The contributor is a female aged 40–49. The lesion is described as raised or bumpy, fluid-filled and rough or flaky. Self-categorized by the patient as a rash. The patient reports the condition has been present for more than one year. The affected area is the leg and arm. An image taken at an angle. The patient also reports chills, fatigue and joint pain. Reported lesion symptoms include enlargement, pain, bleeding, darkening, burning and itching:
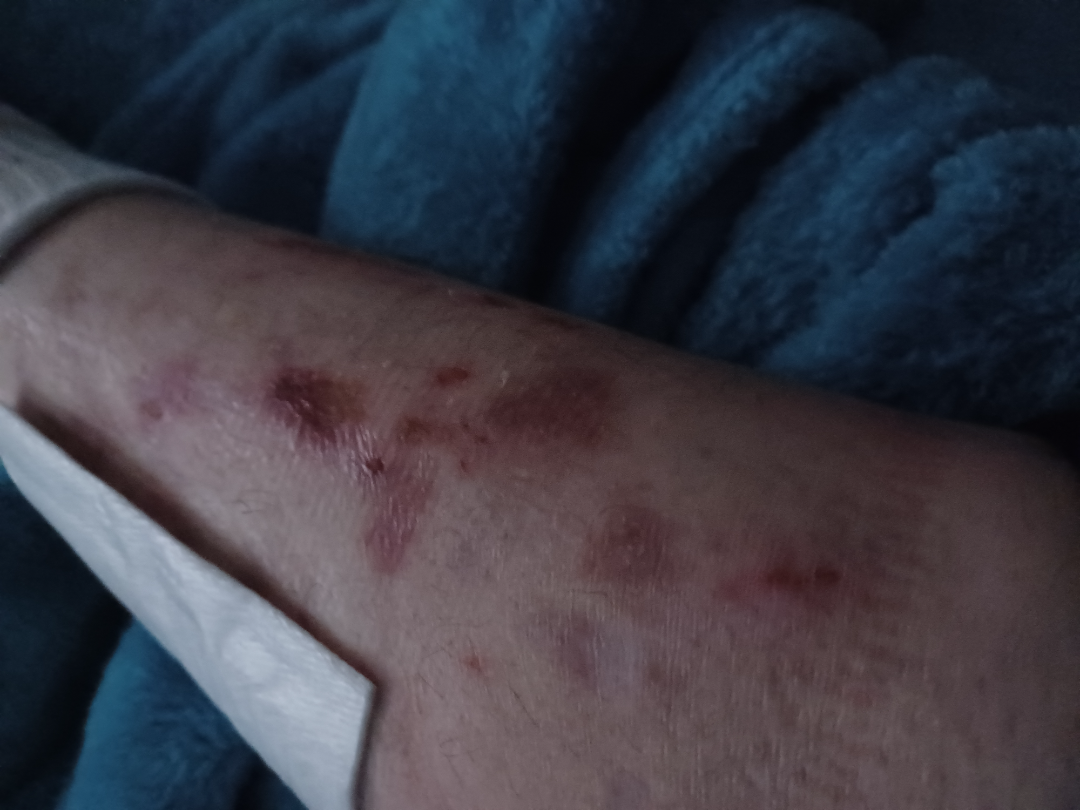| field | value |
|---|---|
| assessment | Abrasion, scrape, or scab and Bullous Pemphigoid were each considered, in no particular order; less probable is ecchymoses; less likely is Eczema |